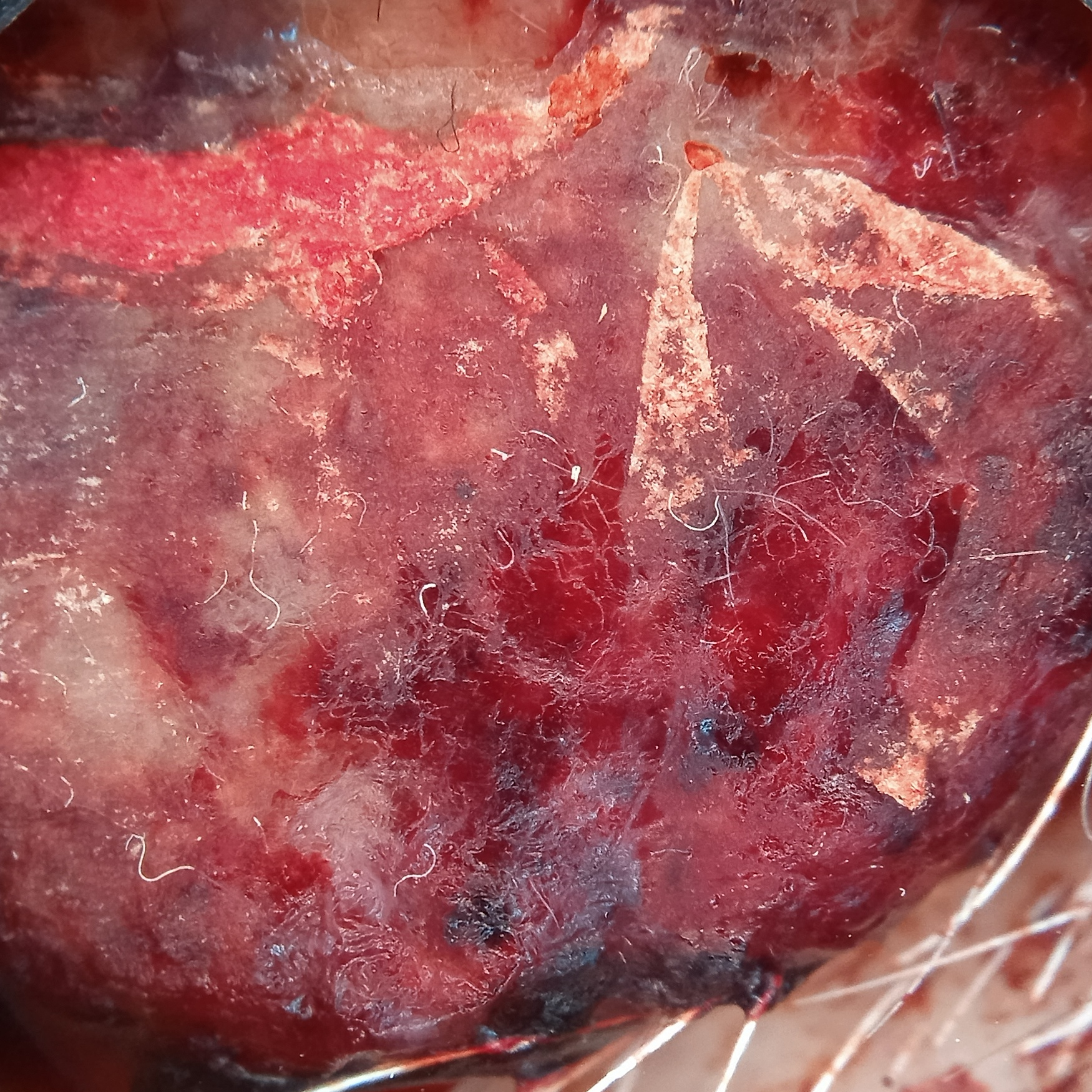The patient reports a personal history of cancer. Dermoscopy of a skin lesion. The lesion is about 19.9 mm across. Confirmed on histopathology as a melanoma, following excision.